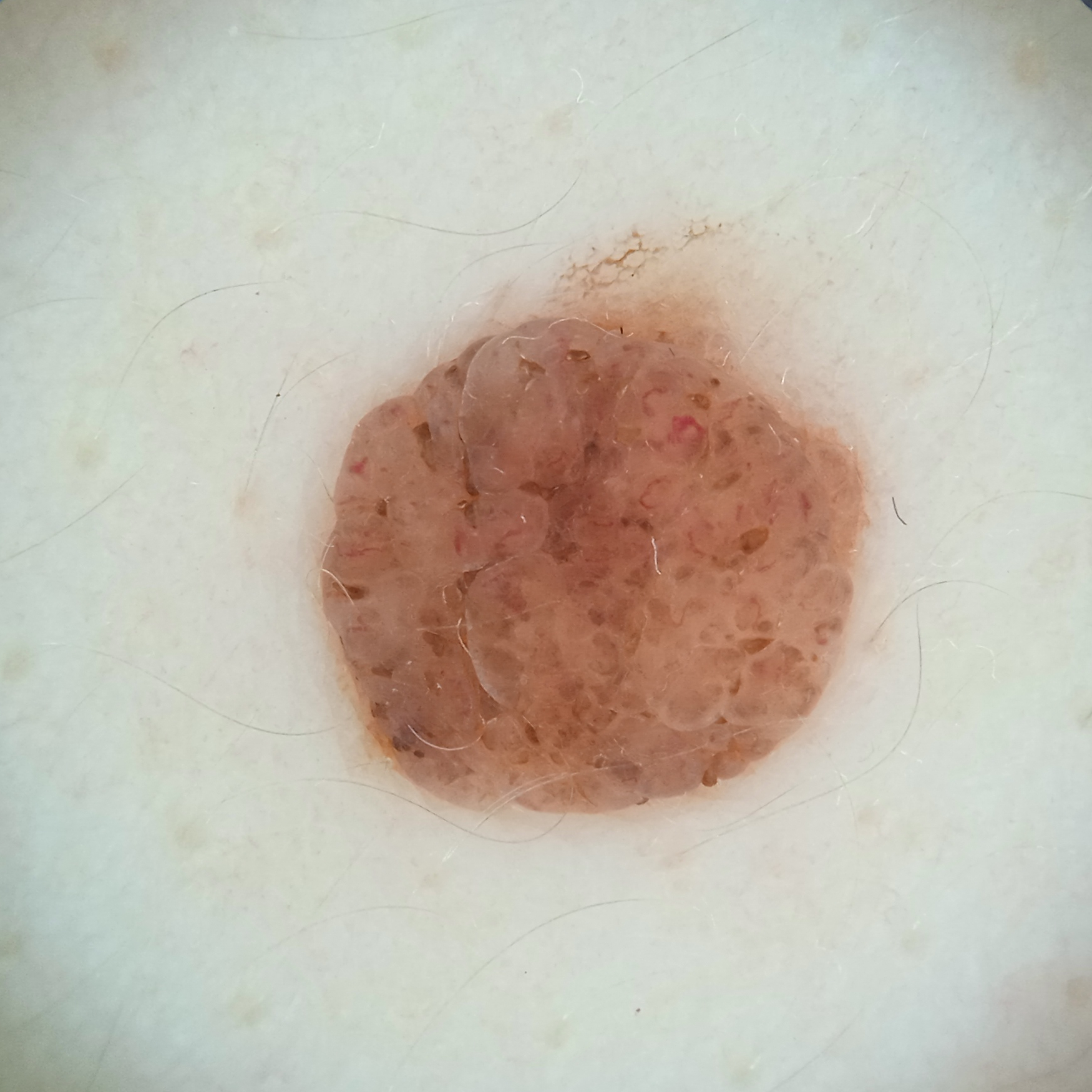{
  "patient": {
    "age": 26,
    "sex": "female"
  },
  "mole_burden": "numerous melanocytic nevi",
  "image": "dermoscopic image",
  "referral": "research study (no referral diagnosis)",
  "sun_reaction": "skin reddens with sun exposure",
  "risk_factors": {
    "positive": [
      "a history of sunbed use"
    ]
  },
  "lesion_location": "the back",
  "lesion_size": {
    "diameter_mm": 5.6
  },
  "diagnosis": {
    "name": "melanocytic nevus",
    "malignancy": "benign"
  }
}